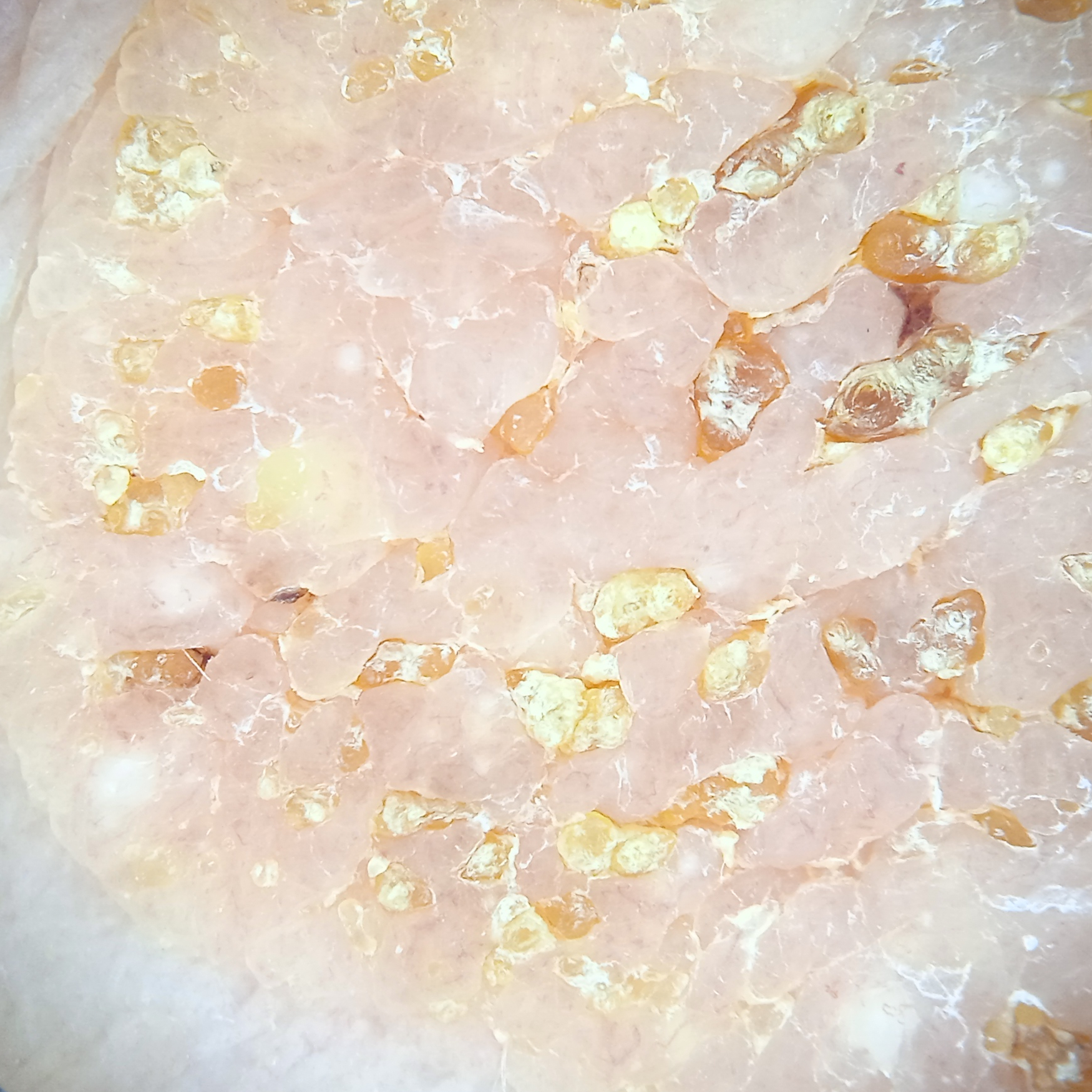A dermoscopy image of a skin lesion. A female subject 81 years of age. Acquired for a research image collection, with no referral diagnosis. Located on the torso. The lesion is about 31 mm across. The consensus diagnosis for this lesion was a seborrheic keratosis.